The patient is a male aged around 65, a dermoscopy image of a single skin lesion.
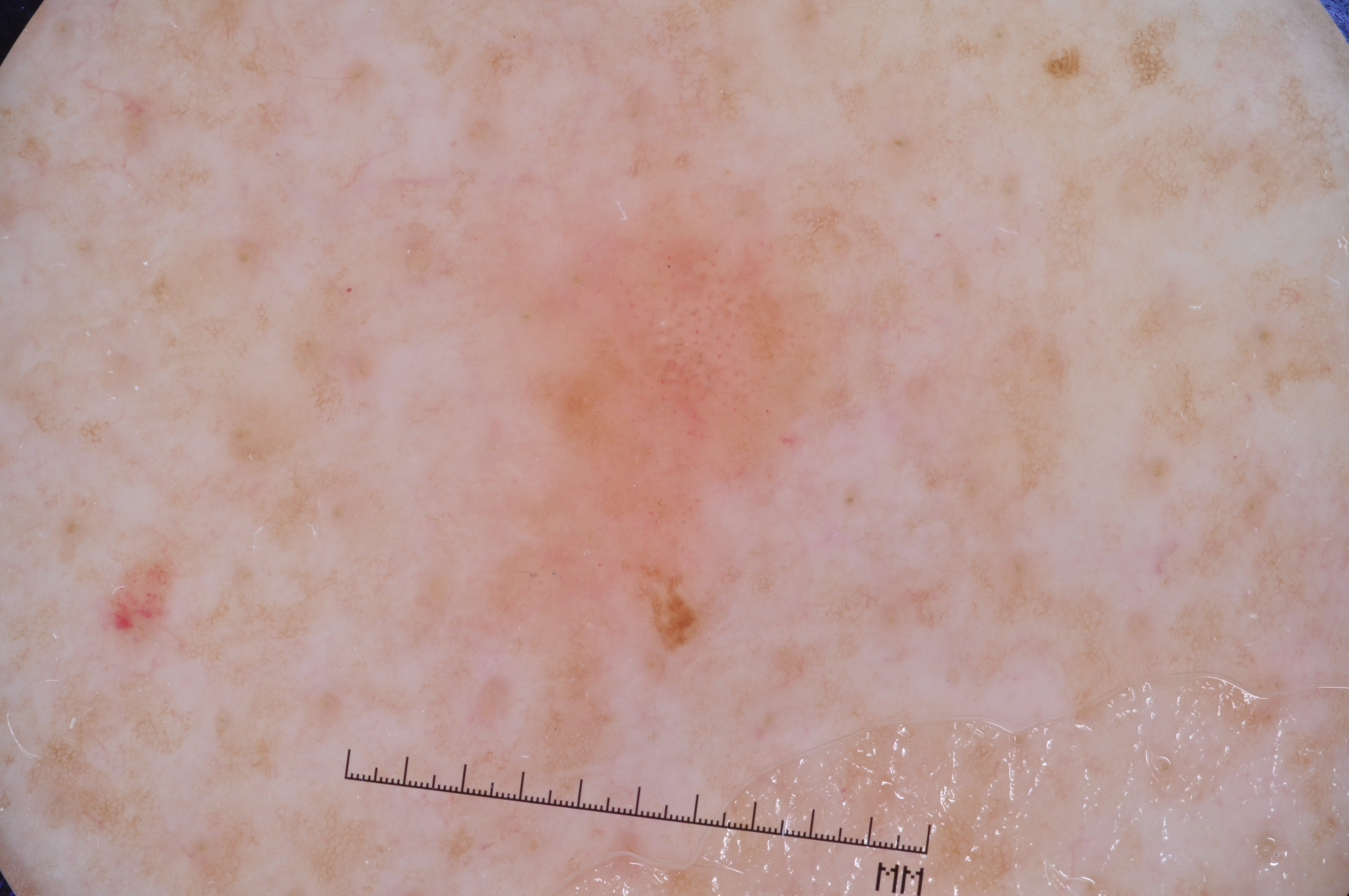Dermoscopic review identifies negative network, milia-like cysts, and pigment network. The visible lesion spans [416,158,868,802]. The lesion takes up a moderate portion of the field. Histopathological examination showed a melanoma.